The photograph is a close-up of the affected area · the lesion involves the front of the torso, arm and head or neck · texture is reported as rough or flaky · the subject is a male aged 40–49 · the patient considered this a rash · the condition has been present for less than one week: 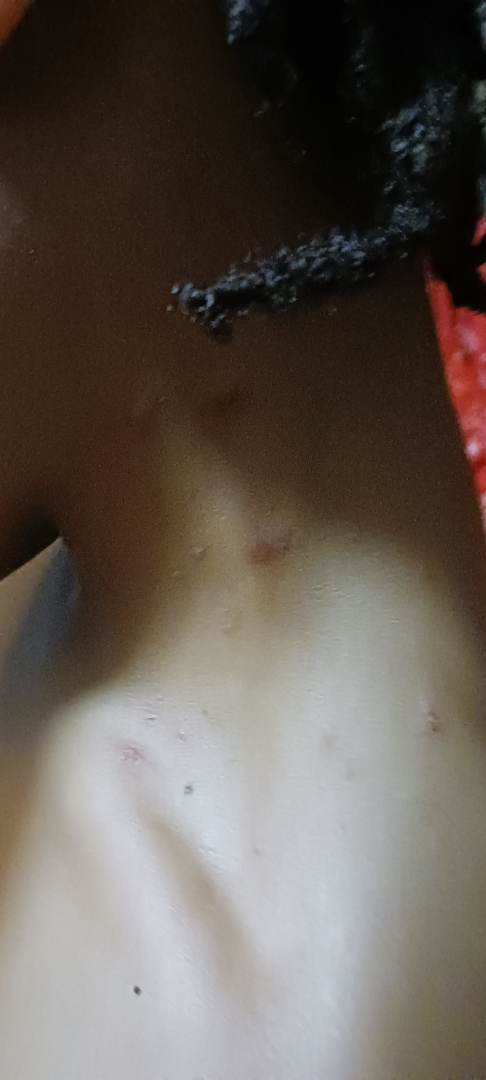Review:
On teledermatology review: Insect Bite (considered); Abscess (considered).